The lesion involves the leg; a close-up photograph; the contributor is 40–49, female — 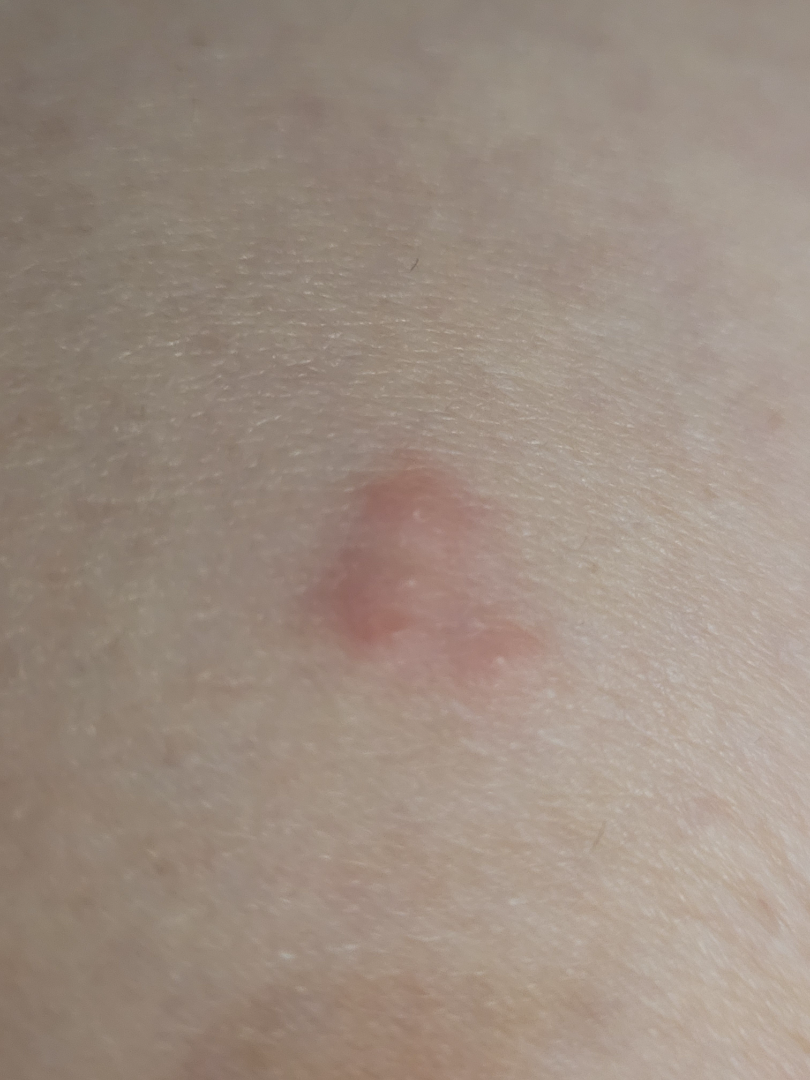Q: What was the assessment?
A: unable to determine